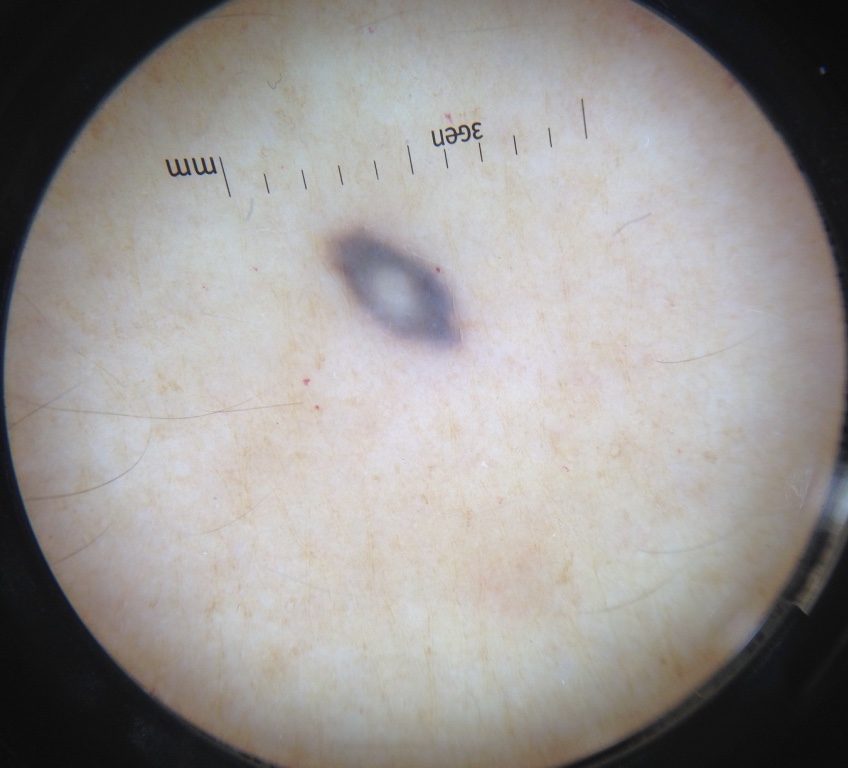Case:
A dermatoscopic image of a skin lesion. The morphology is that of a dermal, banal lesion.
Impression:
Classified as a blue nevus.